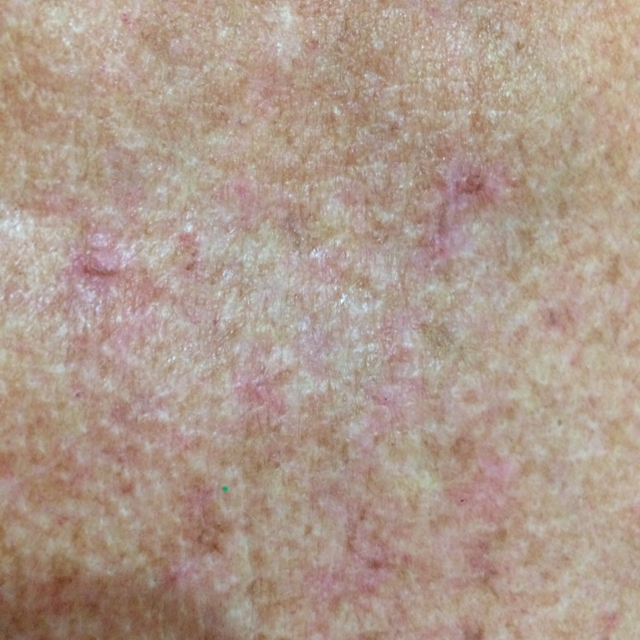Conclusion: Consistent with an actinic keratosis.